A dermoscopic image of a skin lesion: 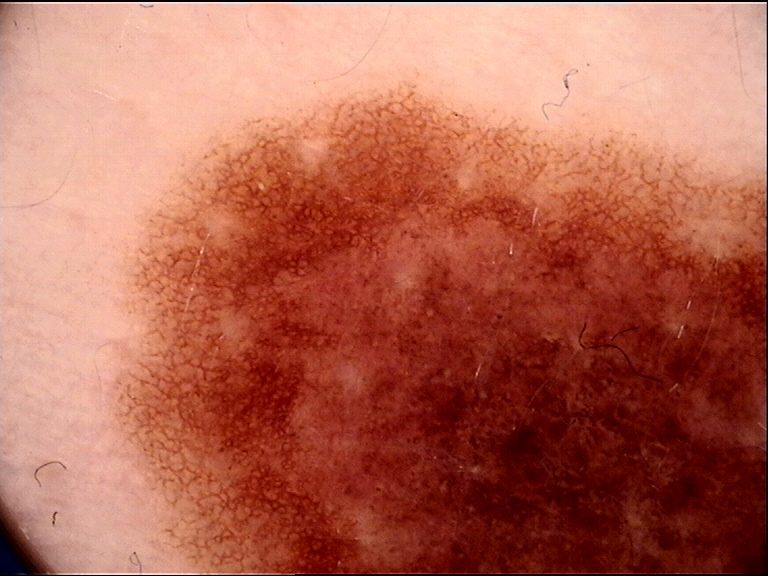{
  "diagnosis": {
    "name": "congenital dysplastic compound nevus",
    "code": "ccd",
    "malignancy": "benign",
    "super_class": "melanocytic",
    "confirmation": "expert consensus"
  }
}